The patient is male. This image was taken at a distance. Located on the leg — 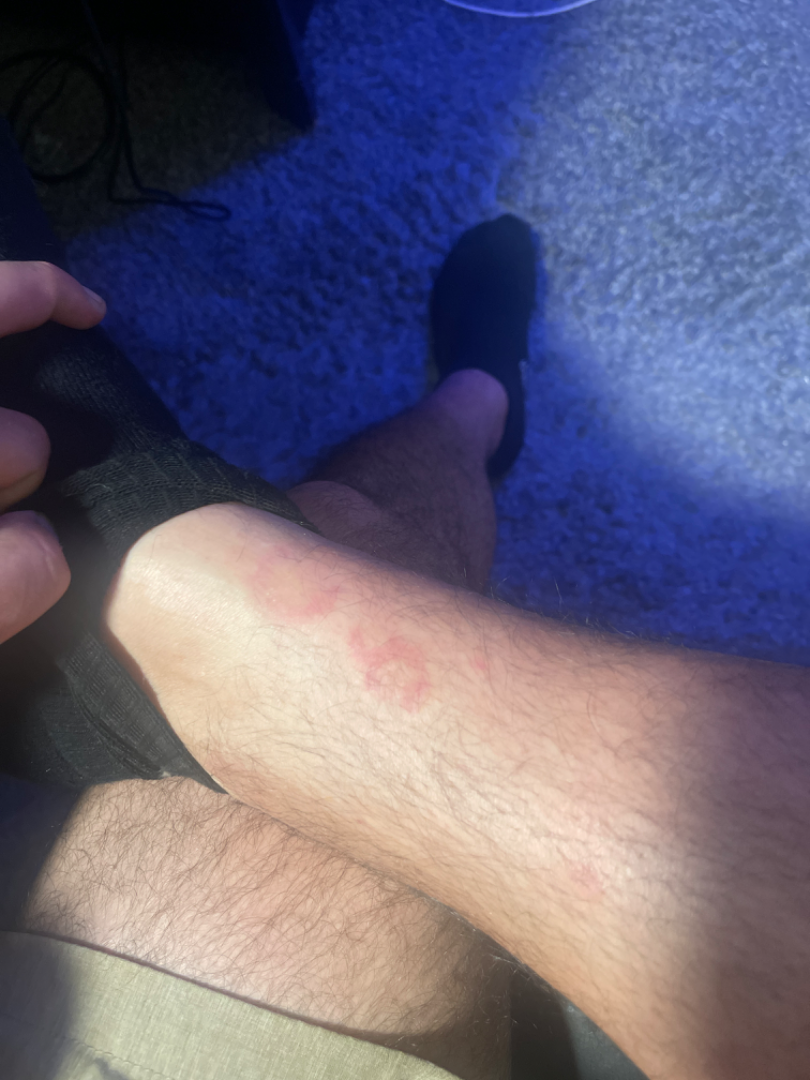assessment: indeterminate.